The affected area is the back of the torso and front of the torso · a close-up photograph.
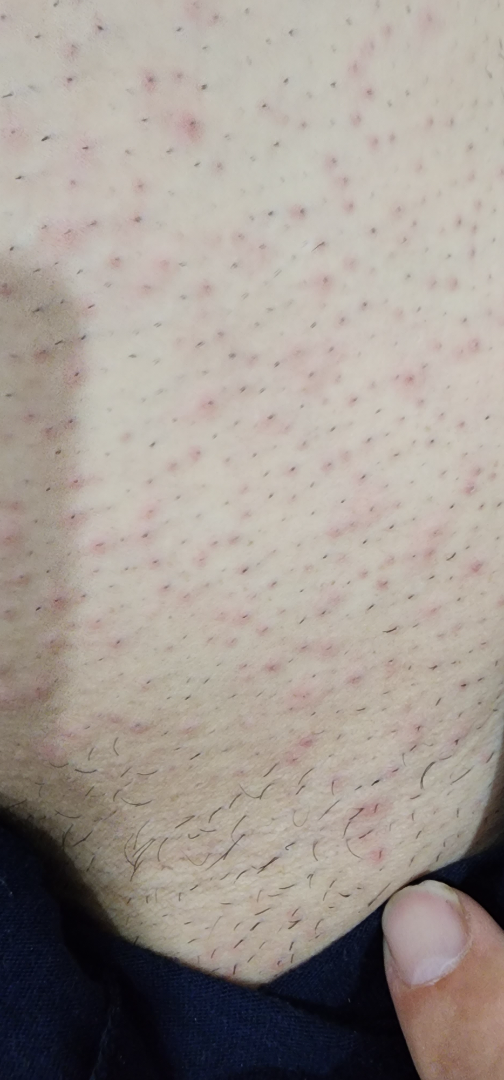assessment: in keeping with Folliculitis.